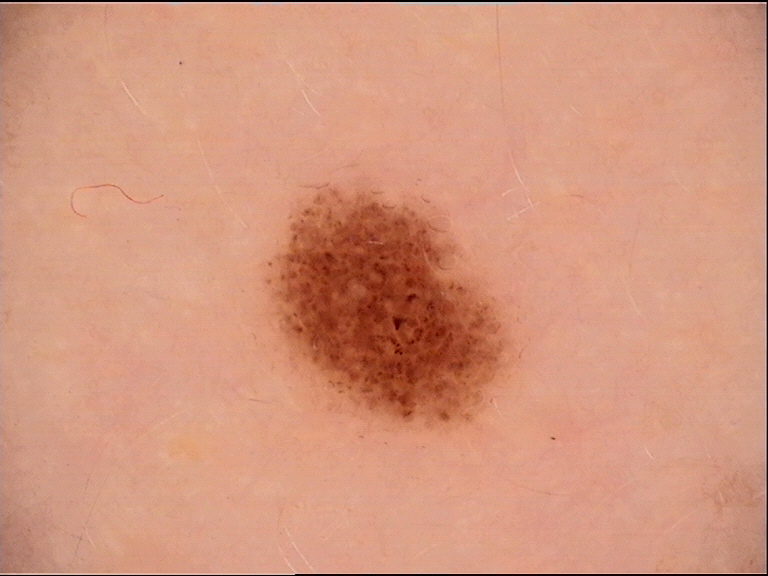The diagnostic label was a dysplastic junctional nevus.